An image taken at an angle; the patient is a male aged 30–39; the palm is involved — 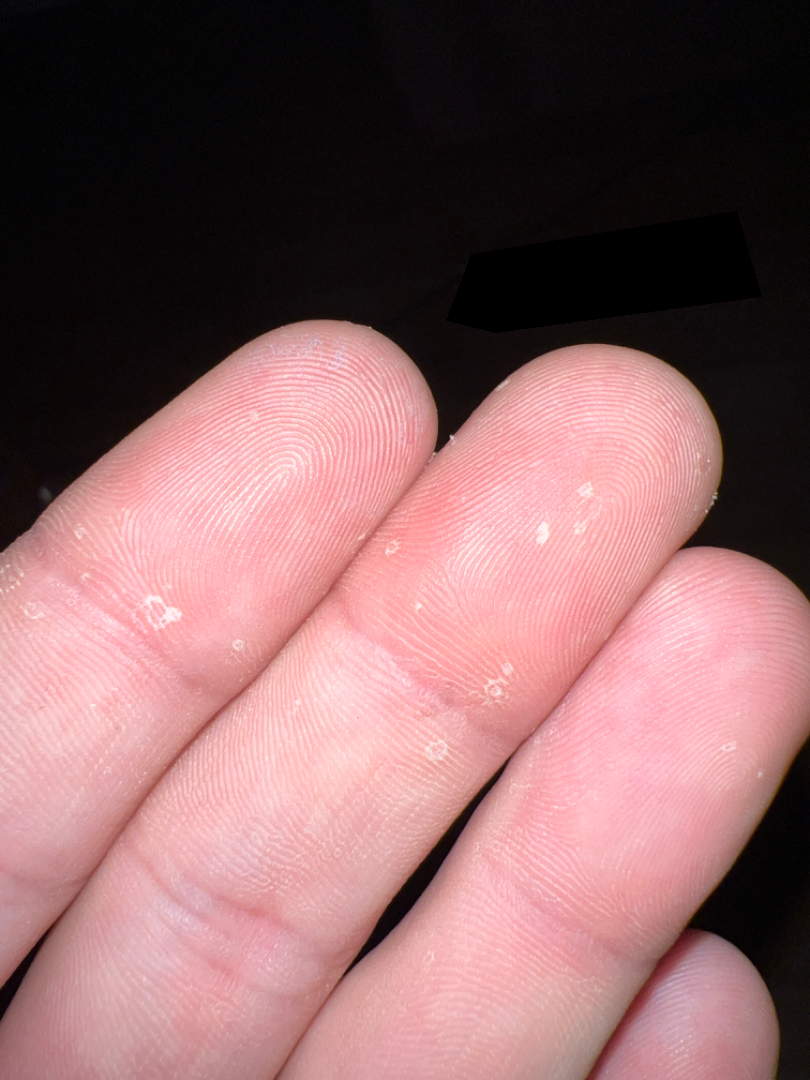Review: No differential diagnosis could be assigned on photographic review.